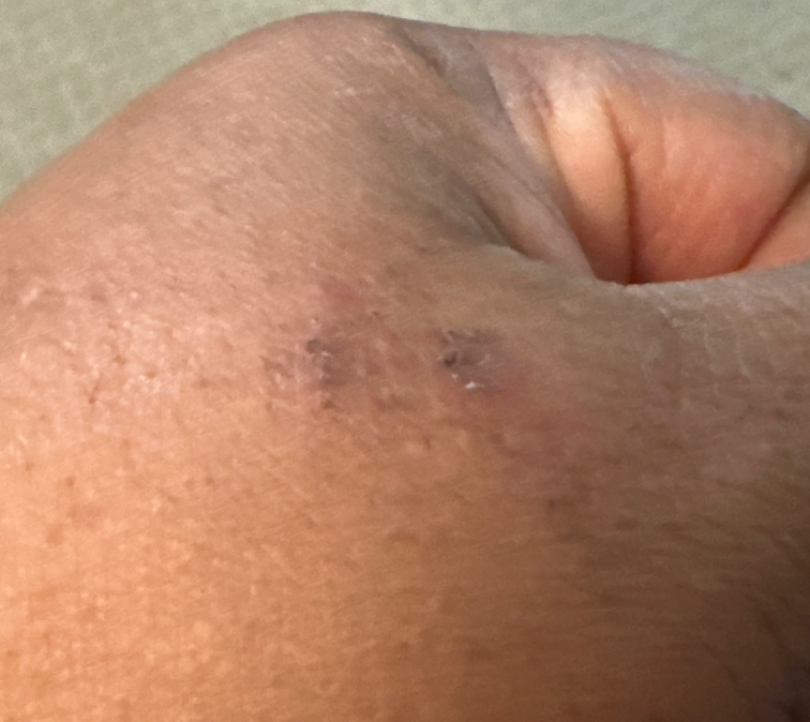Assessment: The case was indeterminate on photographic review. Clinical context: The patient considered this a rash. The lesion is described as raised or bumpy and rough or flaky. A close-up photograph. Reported lesion symptoms include itching. The back of the hand is involved. Reported duration is less than one week.